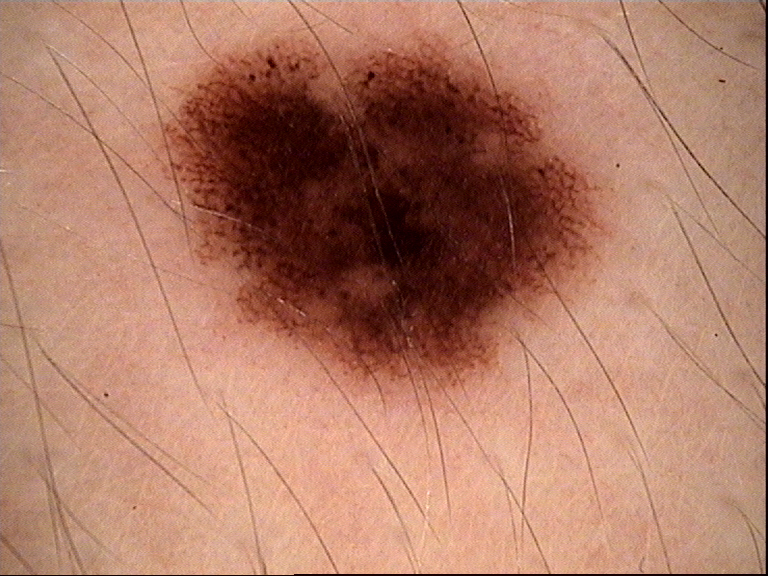A dermoscopic image of a skin lesion.
Consistent with a dysplastic compound nevus.